A male patient 82 years old. A smartphone photograph of a skin lesion. Recorded as FST I. The chart notes alcohol use, pesticide exposure, and prior skin cancer (patient or family):
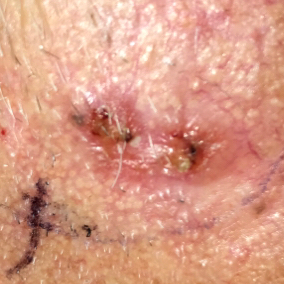Clinical context:
The lesion was found on the face. The lesion measures approximately 22 × 10 mm.
Conclusion:
Biopsy-confirmed as a malignant skin lesion — a basal cell carcinoma.